A dermoscopy image of a single skin lesion:
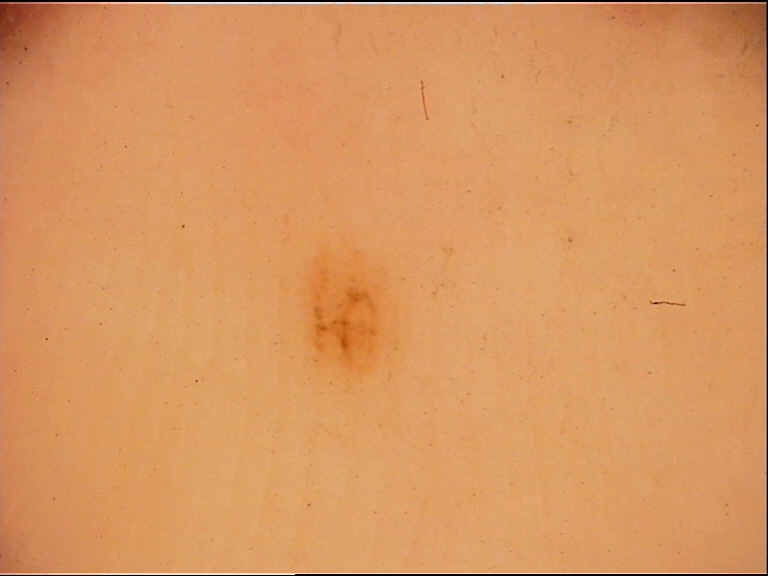category: banal; class: acral junctional nevus (expert consensus).